A skin lesion imaged with a dermatoscope:
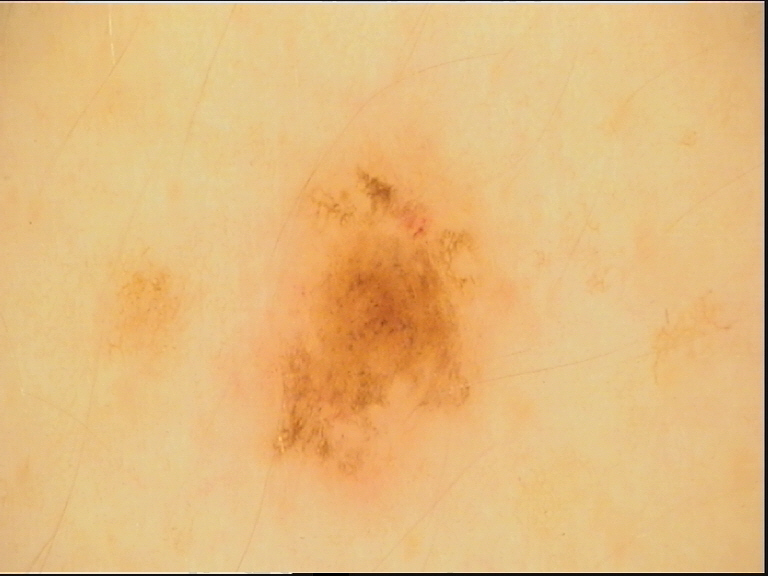  diagnosis:
    name: dysplastic junctional nevus
    code: jd
    malignancy: benign
    super_class: melanocytic
    confirmation: expert consensus